The chart records melanoma in a first-degree relative. Recorded as skin type III.
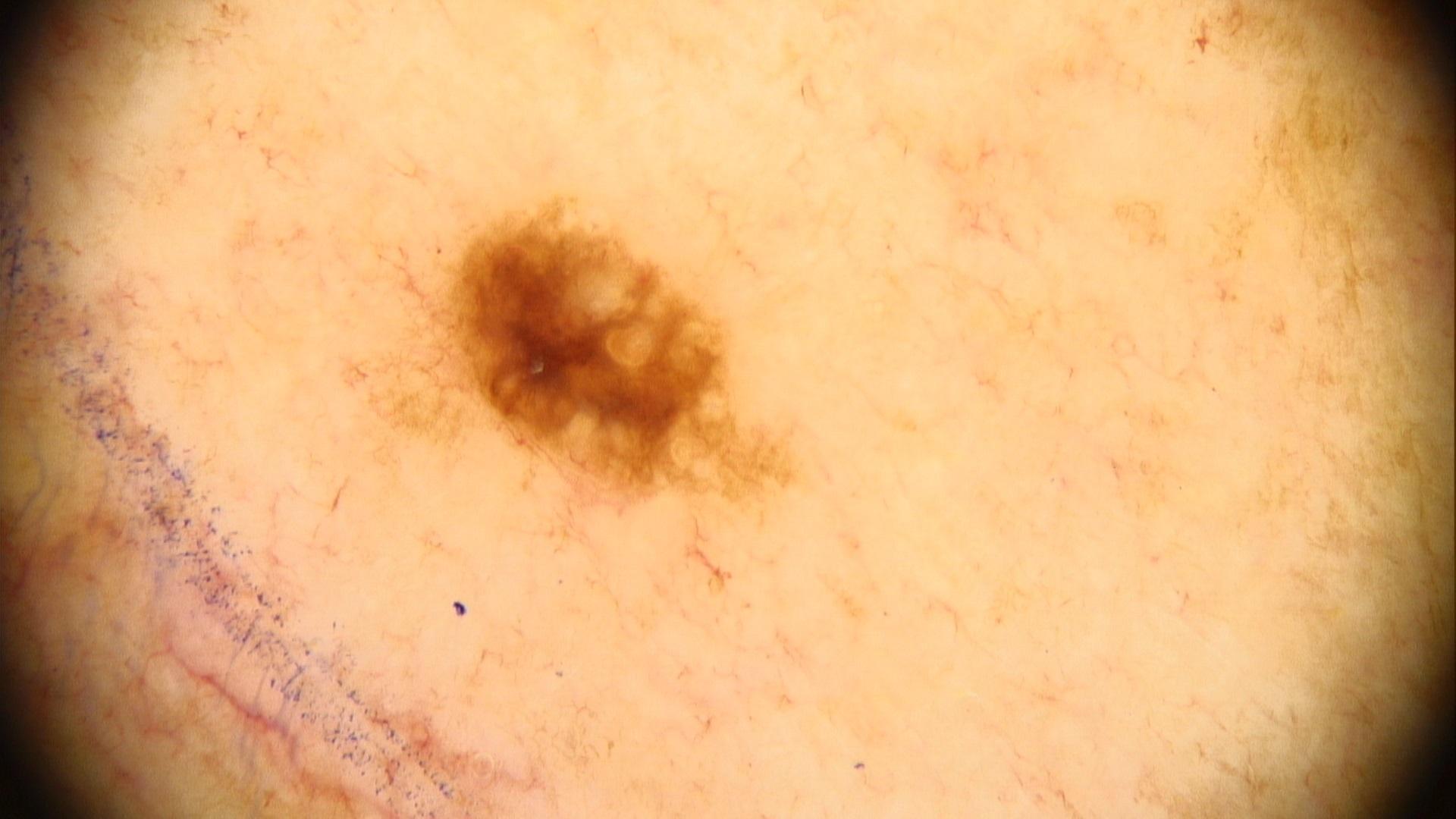Q: Where on the body is the lesion?
A: the trunk (the anterior trunk)
Q: What was the clinical impression?
A: Nevus